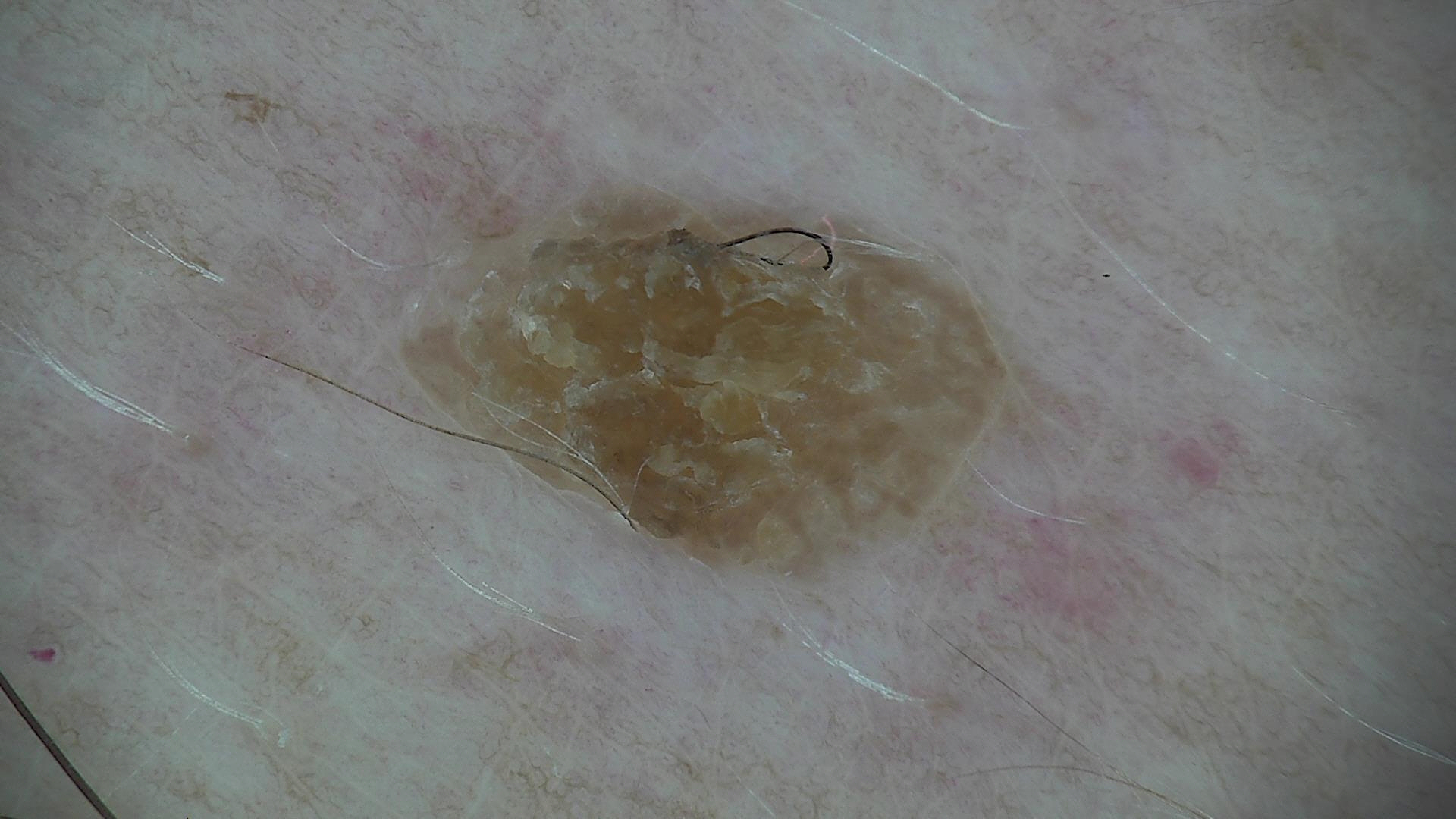The architecture is that of a keratinocytic lesion.
Diagnosed as a seborrheic keratosis.